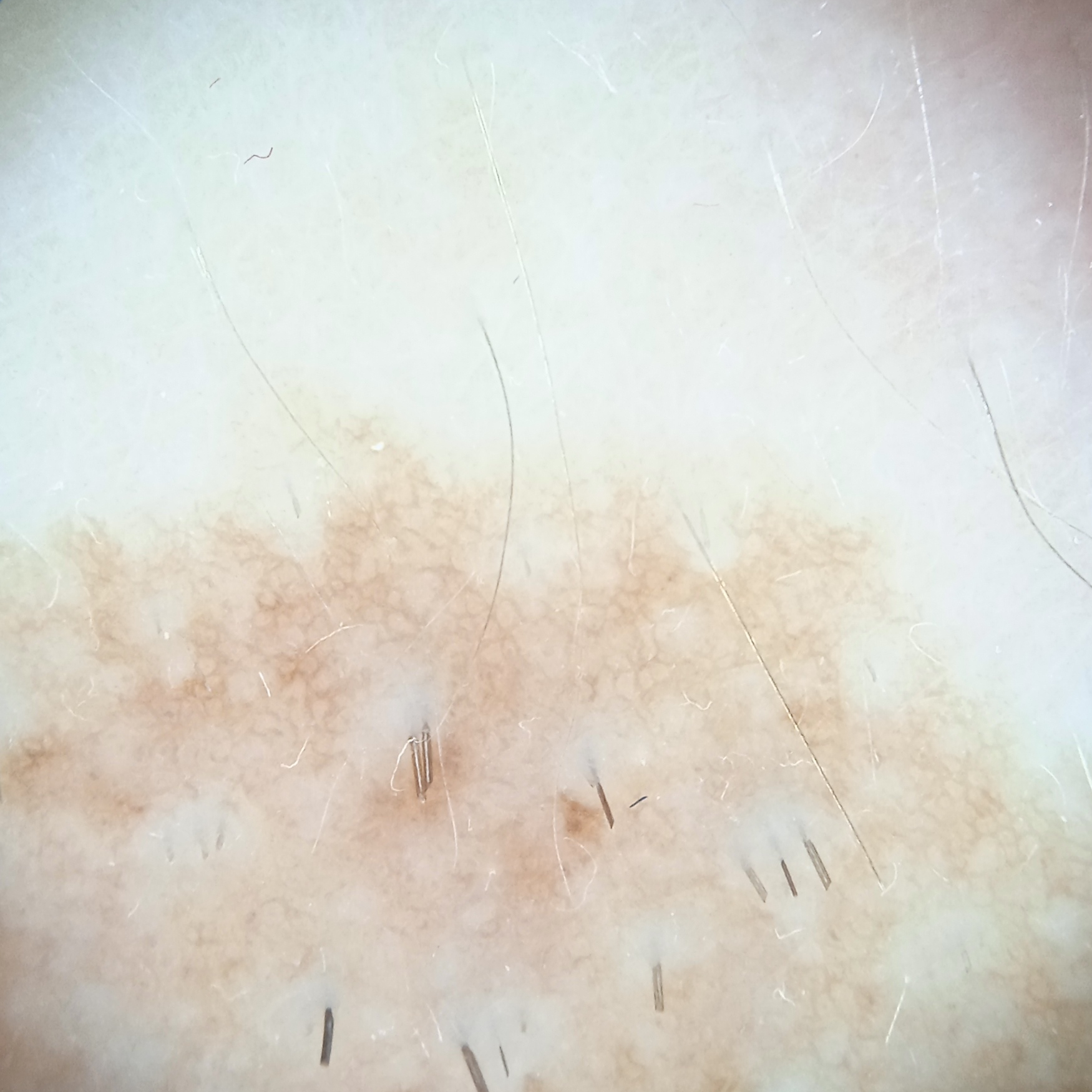The patient describes having few moles overall. The lesion is located on an arm. Histopathology confirmed a melanocytic nevus, following a punch biopsy.